A dermoscopic close-up of a skin lesion.
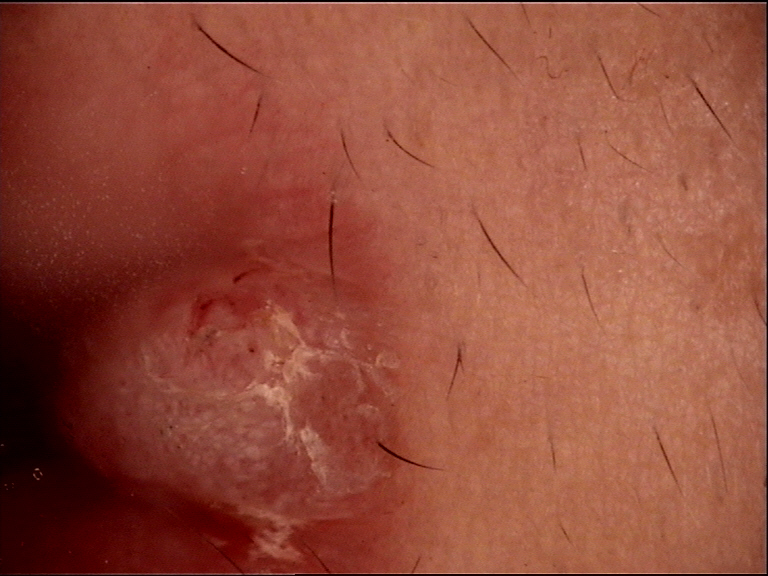subtype: keratinocytic | class: squamous cell carcinoma (biopsy-proven).